A dermoscopic image of a skin lesion.
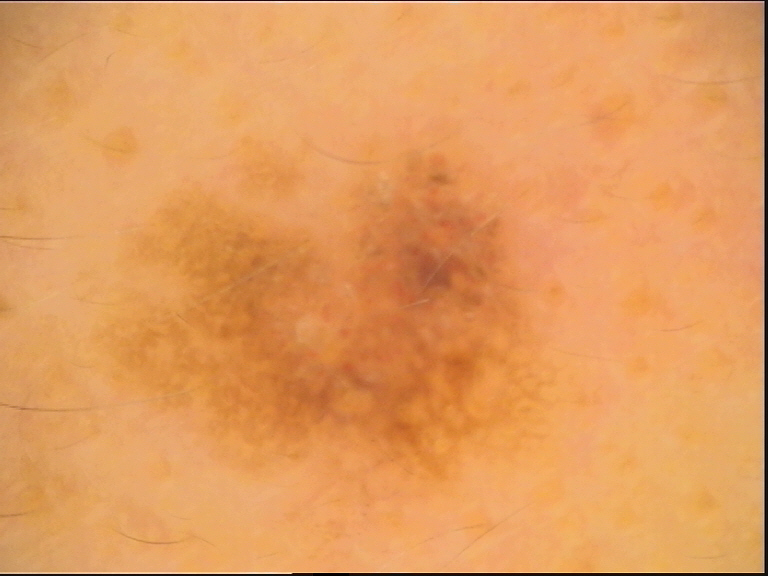Case:
The morphology is that of a keratinocytic lesion.
Conclusion:
Diagnosed as a seborrheic keratosis.